This is a dermoscopic photograph of a skin lesion · a female subject, approximately 45 years of age — 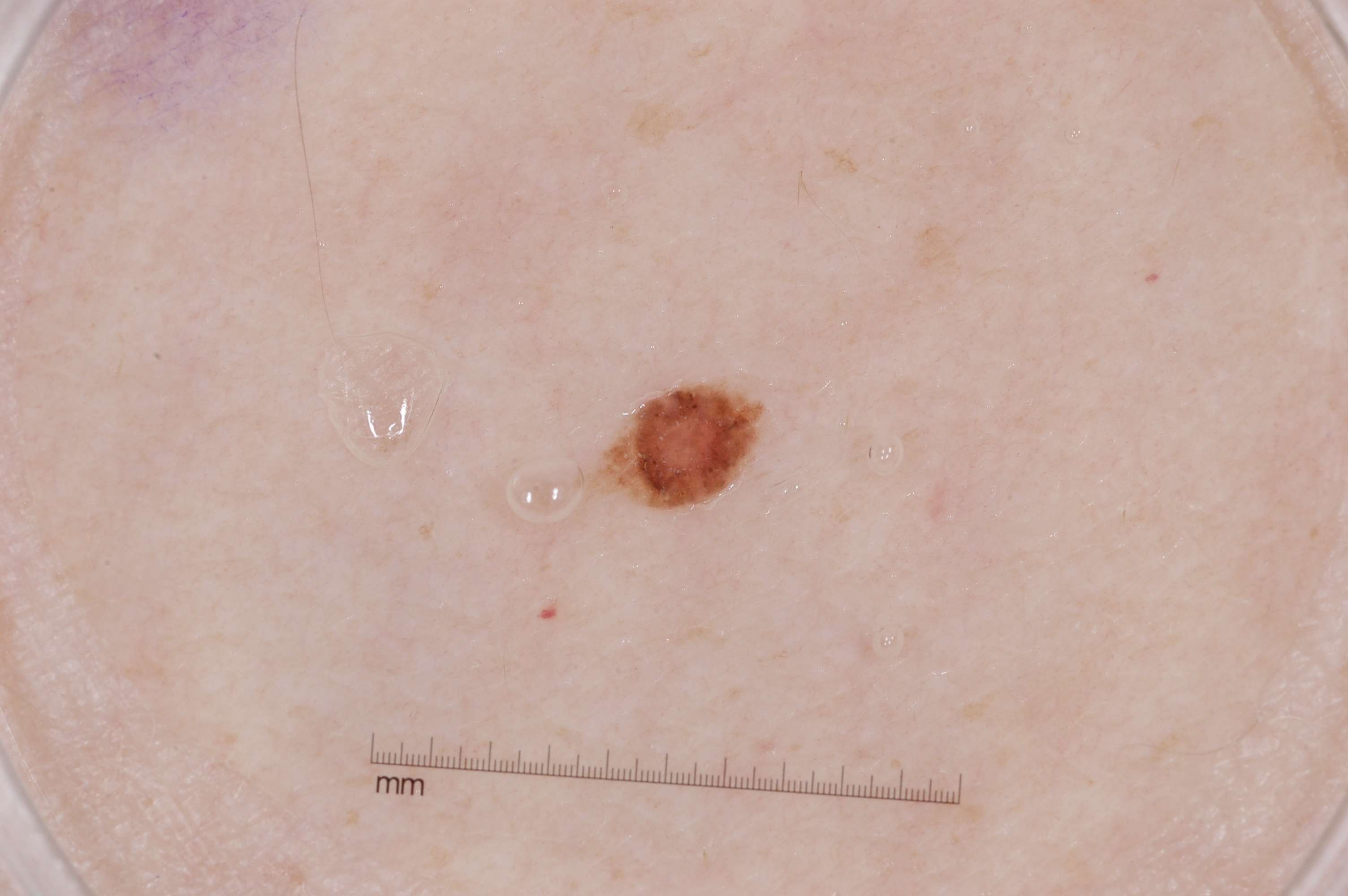Image and clinical context: Dermoscopic assessment notes no negative network, streaks, milia-like cysts, or pigment network. The lesion is bounded by left=611, top=385, right=758, bottom=504. Impression: Consistent with a melanocytic nevus, a benign lesion.